A dermatoscopic image of a skin lesion.
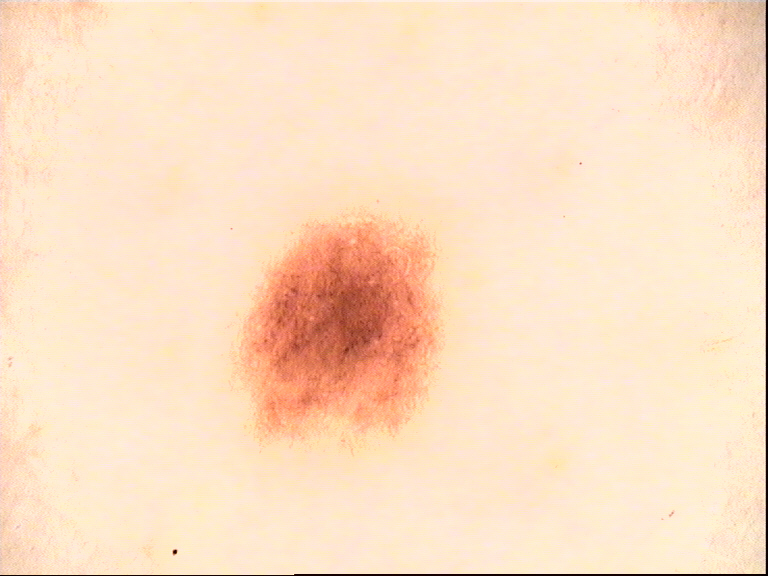Diagnosed as a dysplastic junctional nevus.